Located on the head or neck, arm, palm, front of the torso, back of the torso and back of the hand · female contributor, age 18–29 · a close-up photograph.
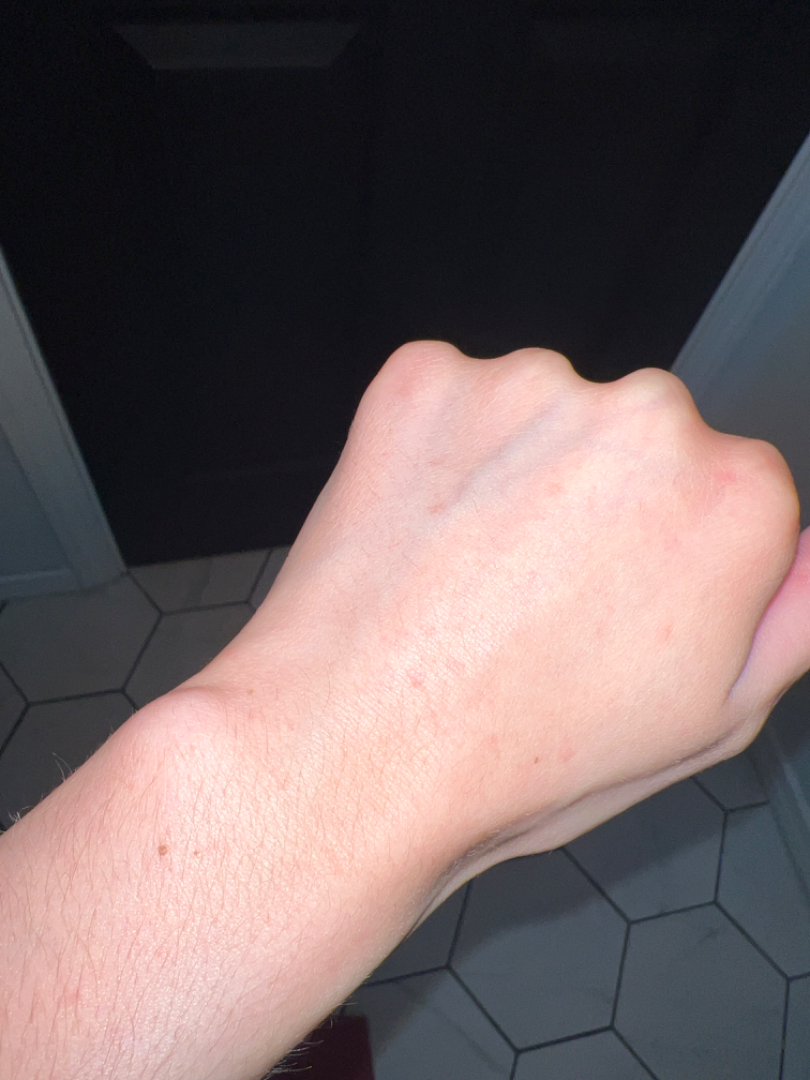Impression: On dermatologist assessment of the image, in keeping with Insect Bite.